Located on the arm. Texture is reported as rough or flaky. The photograph was taken at a distance — 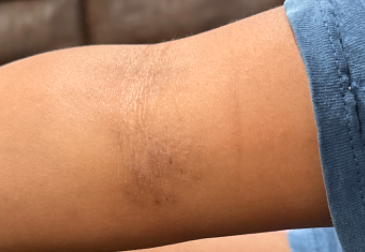On remote review of the image: Eczema (weight 1.00).